The photo was captured at a distance. The patient is female:
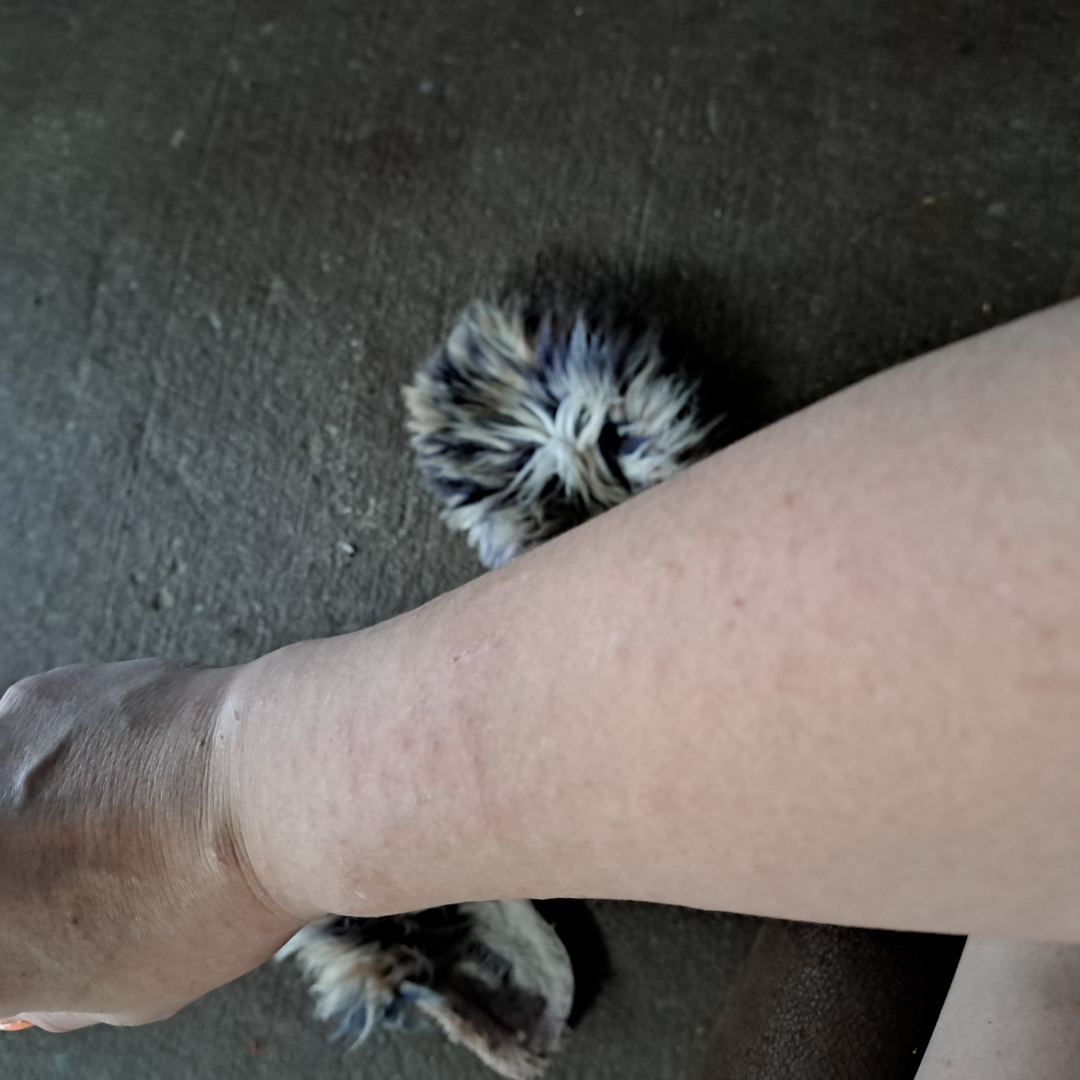Review:
The reviewing dermatologist's impression was: Eczema (primary).